A female patient aged approximately 85 or older.
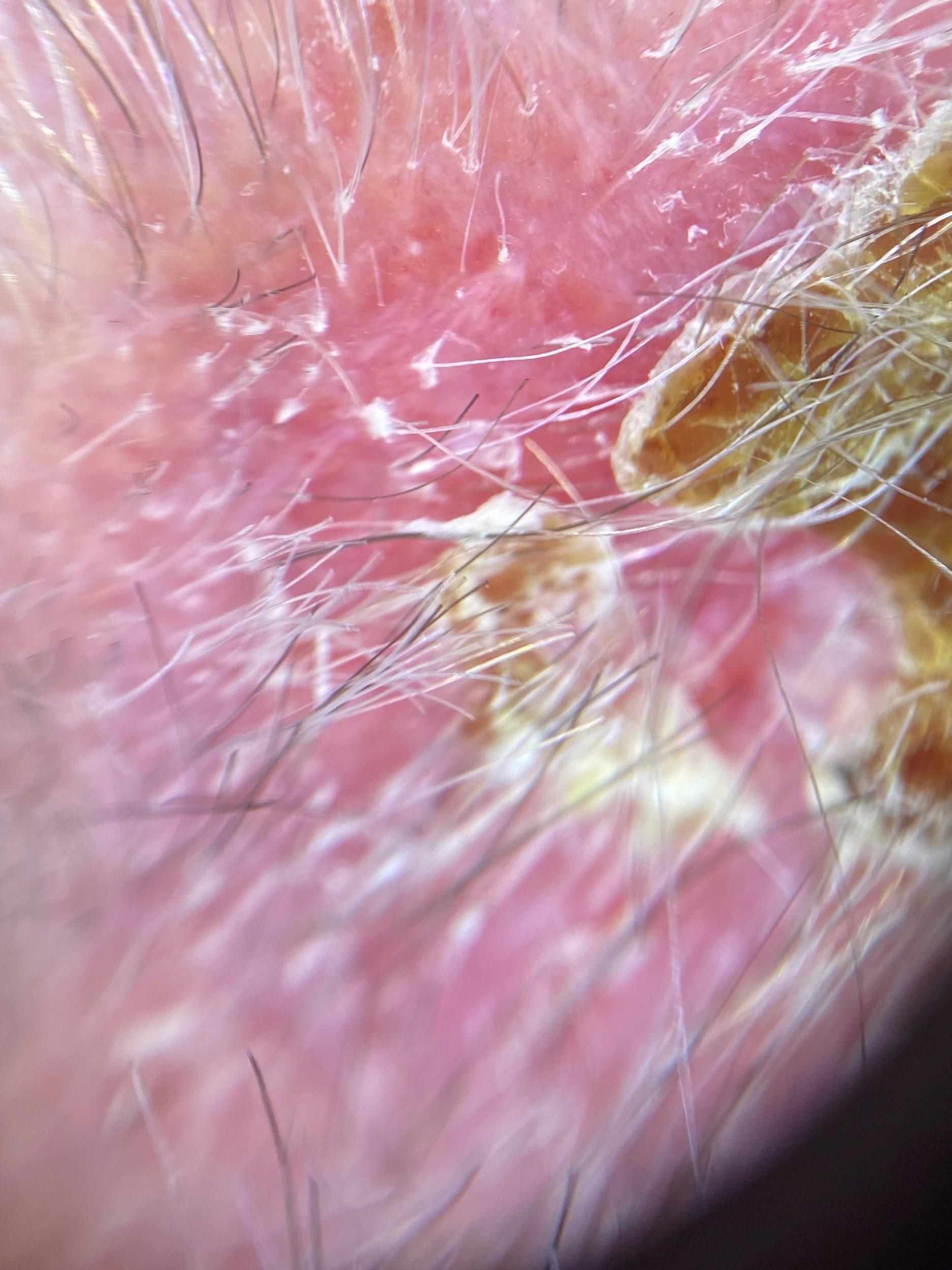The lesion was found on the head or neck.
On biopsy, the diagnosis was a squamous cell carcinoma.